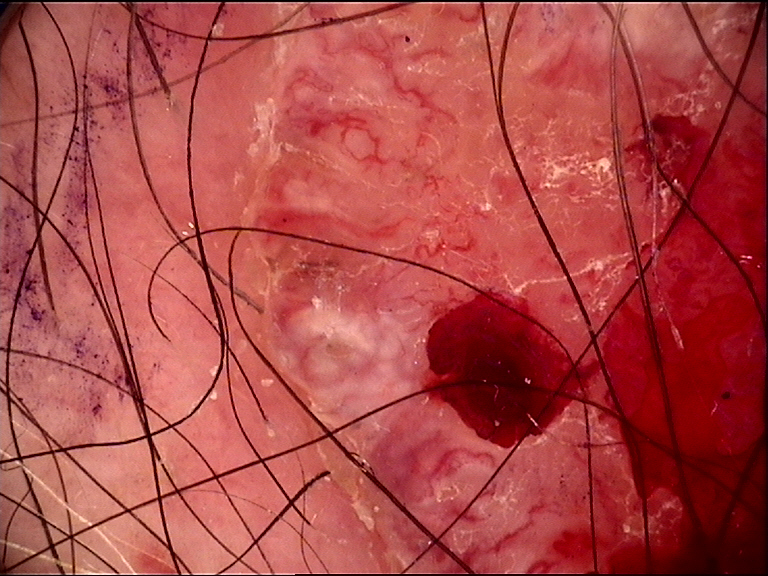Findings: A dermoscopic photograph of a skin lesion. The architecture is that of a keratinocytic lesion. Conclusion: Histopathologically confirmed as a basal cell carcinoma.